The affected area is the arm · the contributor notes the condition has been present for less than one week · the photograph is a close-up of the affected area · Fitzpatrick III; lay graders estimated Monk Skin Tone 3 or 4.
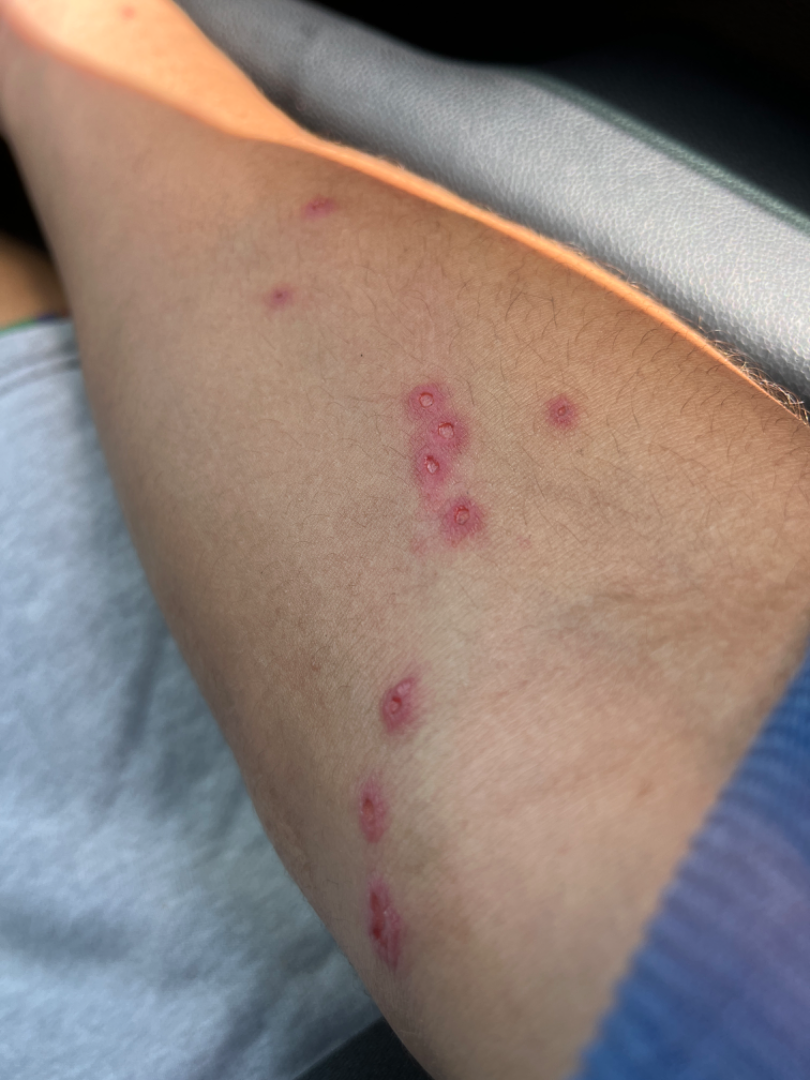- assessment: the leading consideration is Insect Bite; the differential also includes Herpes Simplex; also raised was Allergic Contact Dermatitis